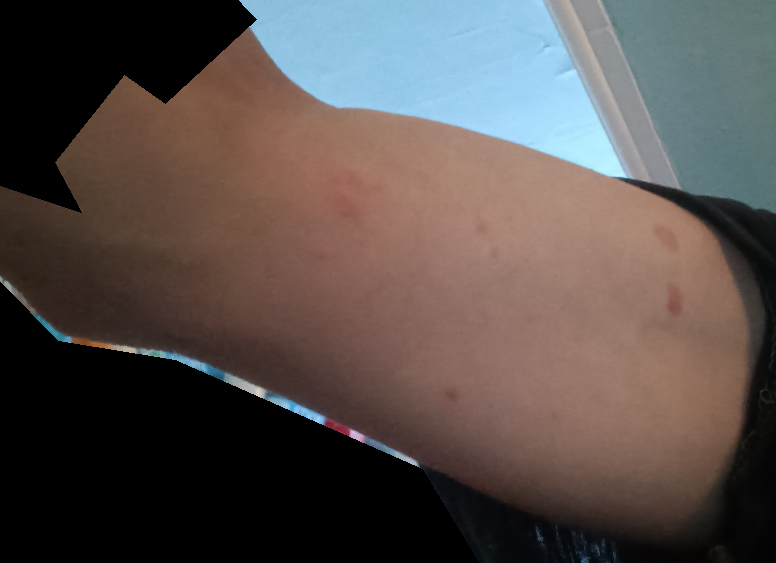assessment = indeterminate
photo taken = close-up